The affected area is the head or neck, arm and front of the torso; the contributor is 40–49, female; a close-up photograph — 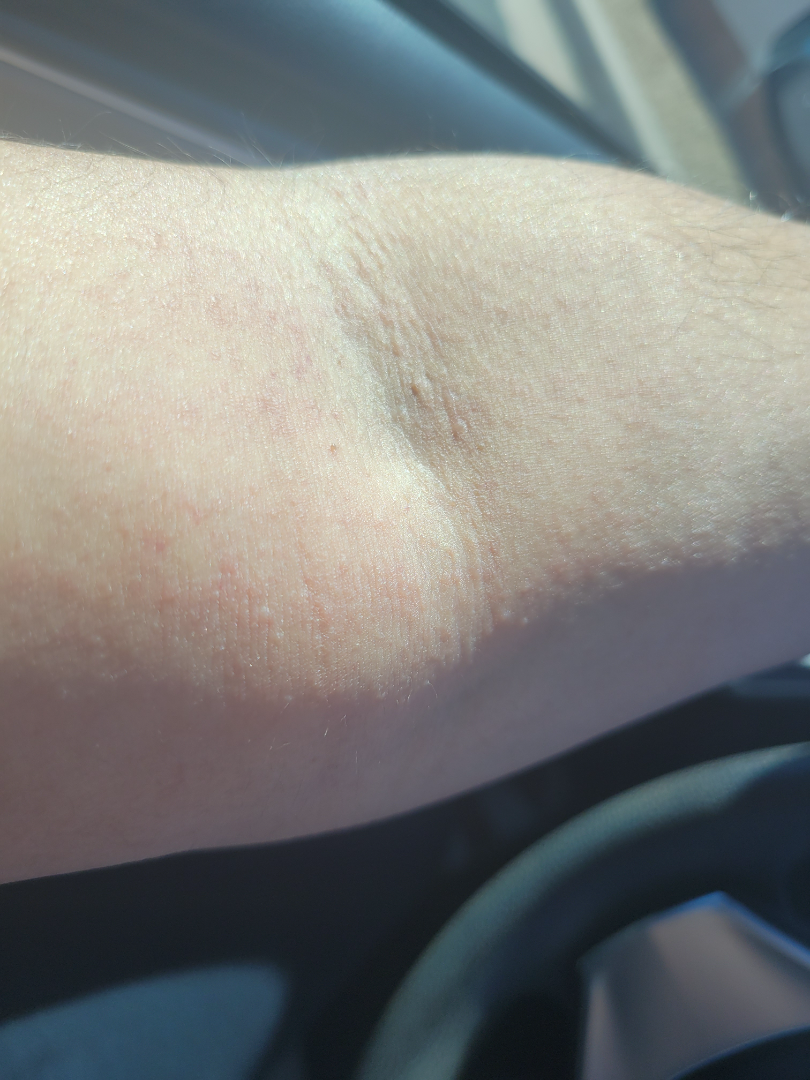Q: Could the case be diagnosed?
A: could not be assessed
Q: Patient's own categorization?
A: a rash
Q: Reported symptoms?
A: itching and bothersome appearance
Q: Constitutional symptoms?
A: none reported
Q: How long has this been present?
A: about one day
Q: How does the lesion feel?
A: raised or bumpy